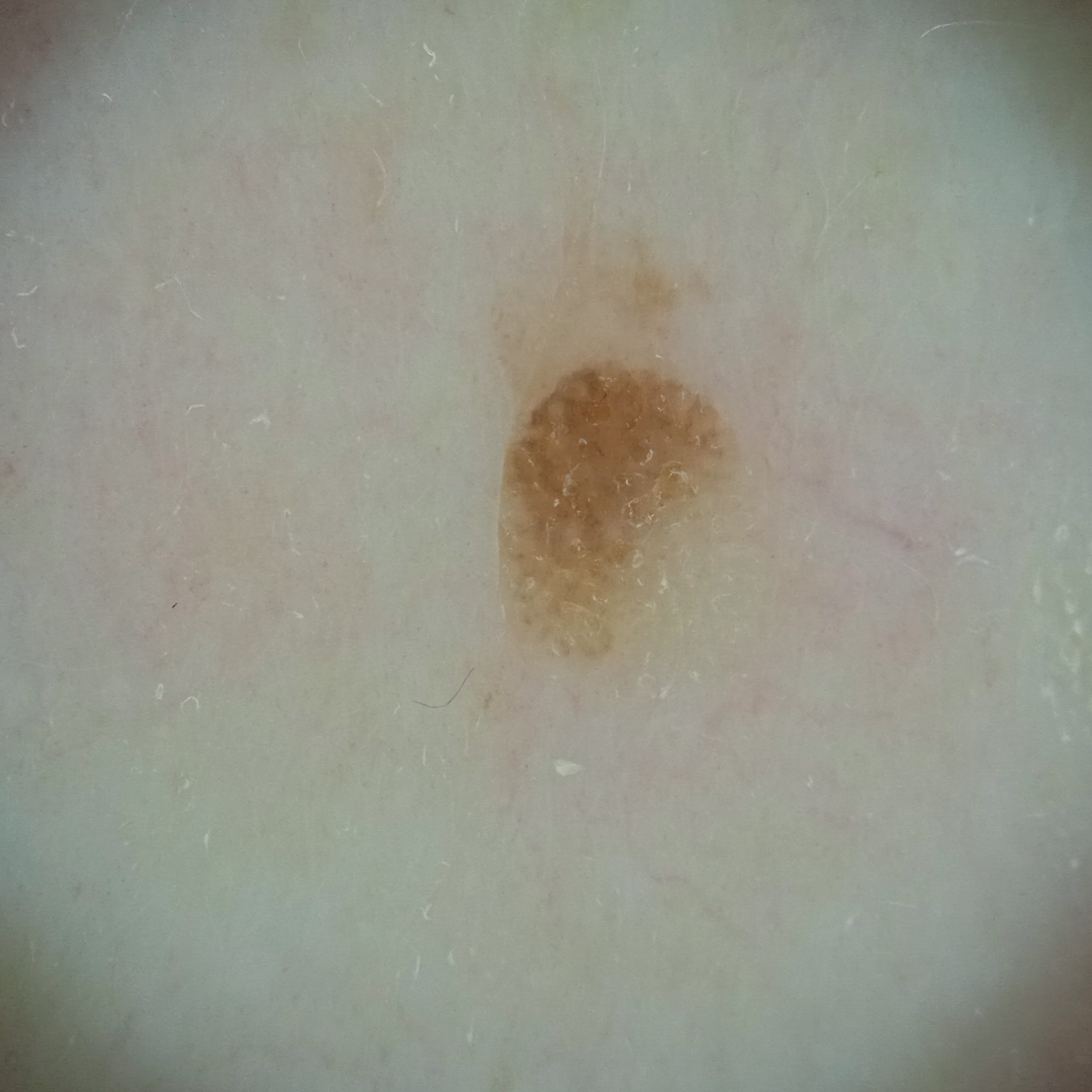A skin lesion imaged with a dermatoscope.
Acquired for a research image collection, with no referral diagnosis.
A male subject aged 77.
Located on the back.
The lesion measures approximately 3 mm.
The lesion was assessed as a seborrheic keratosis.